Dermoscopy of a skin lesion. The patient describes having numerous moles. Collected as part of a research study, without a referral diagnosis: 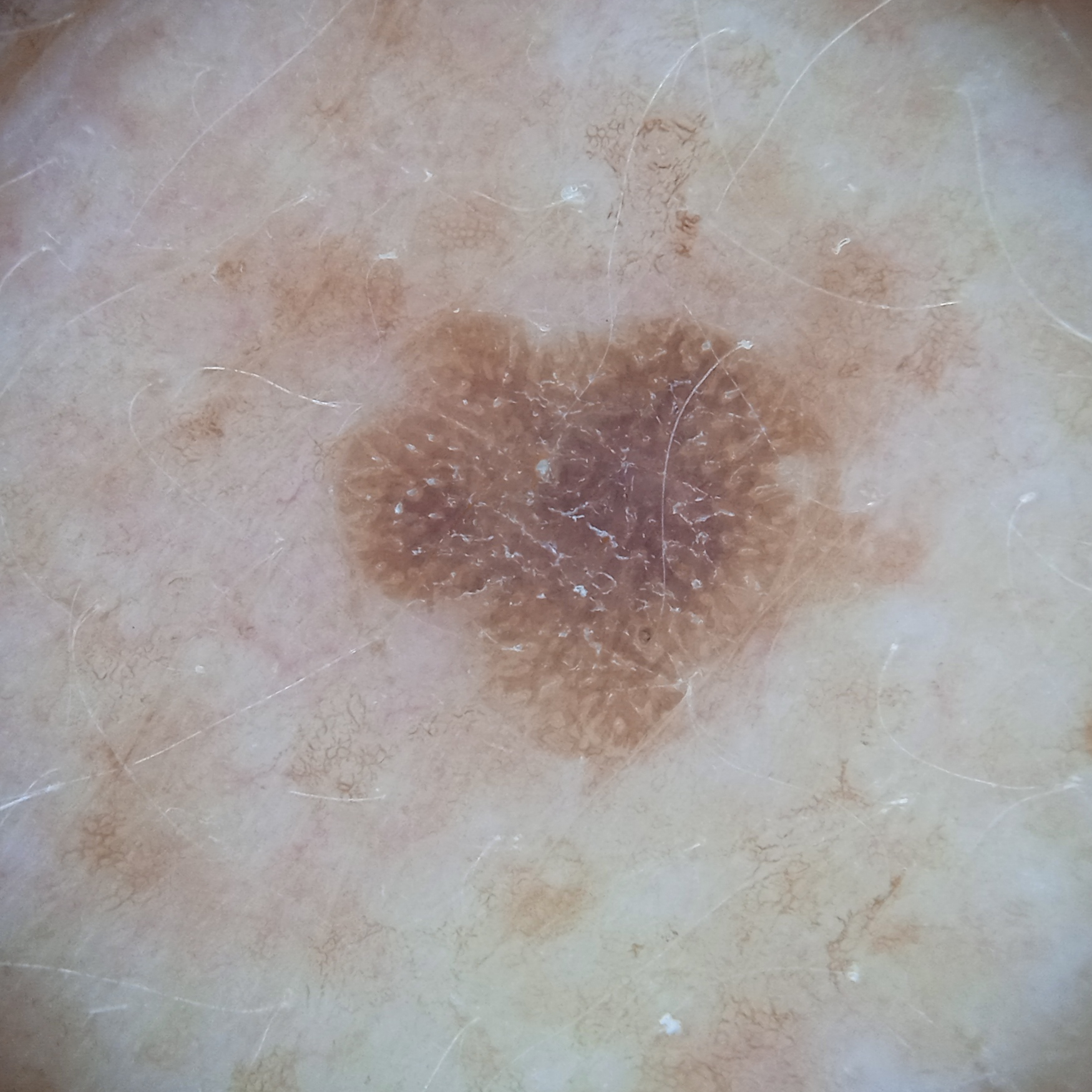Findings:
- body site · the back
- assessment · seborrheic keratosis (dermatologist consensus)